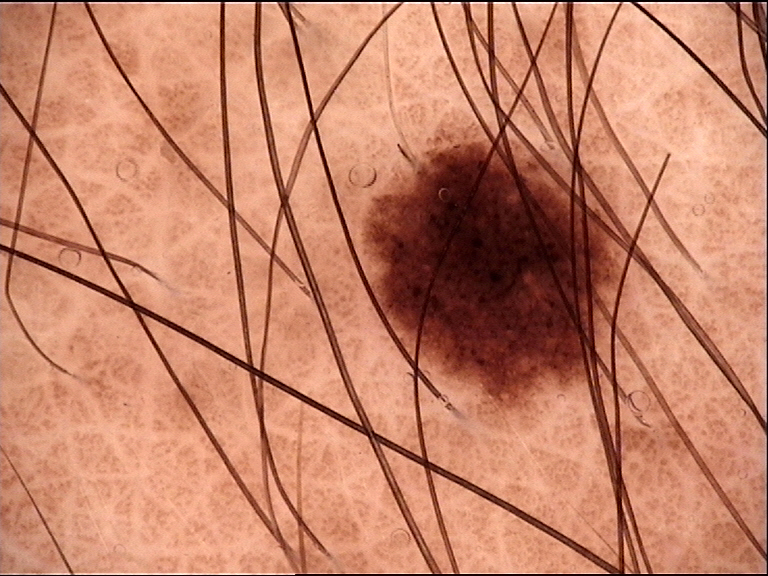Findings:
- modality · dermoscopy
- assessment · dysplastic junctional nevus (expert consensus)